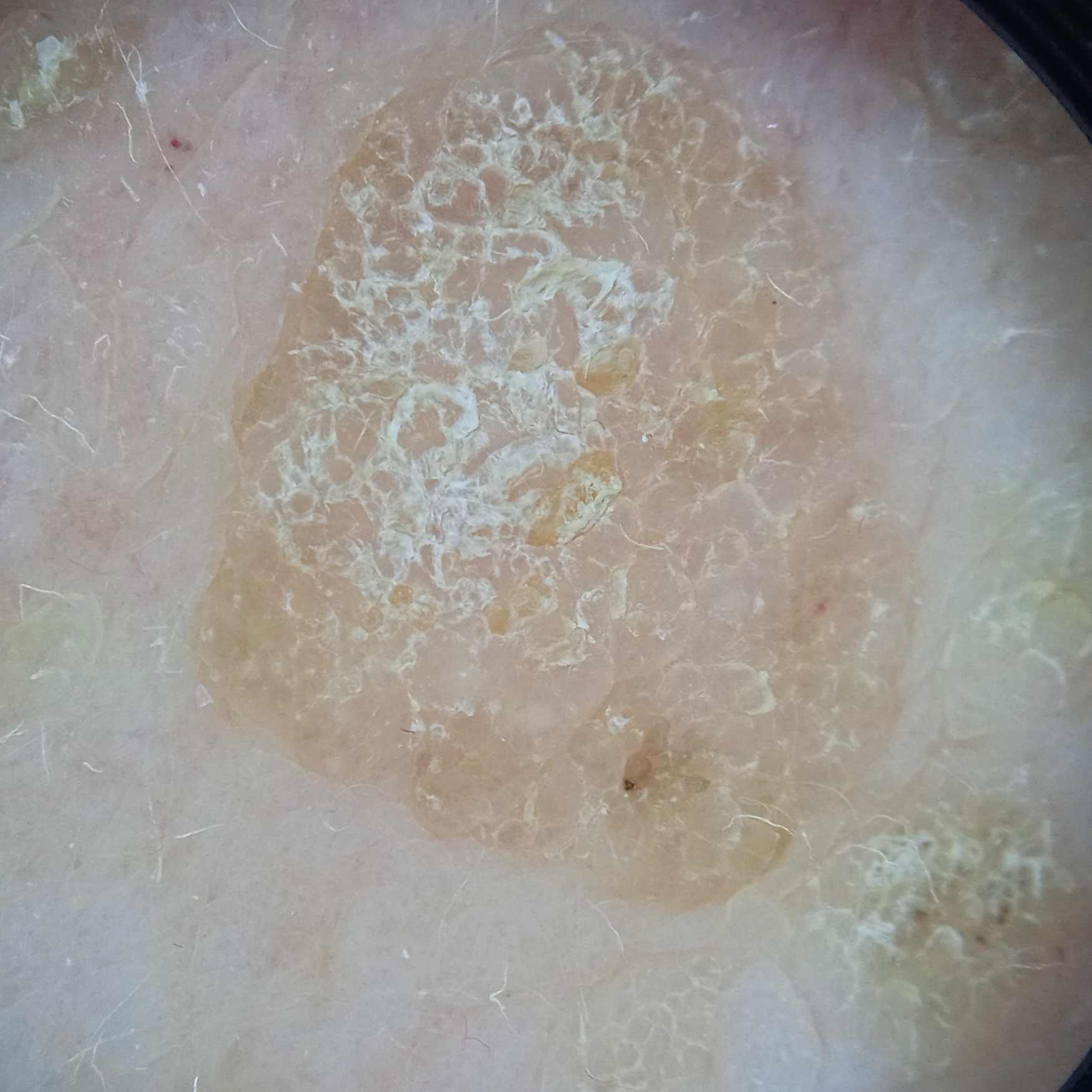{
  "patient": {
    "age": 55,
    "sex": "female"
  },
  "mole_burden": "a moderate number of melanocytic nevi",
  "image": "dermoscopic image",
  "sun_reaction": "skin reddens painfully with sun exposure",
  "risk_factors": {
    "positive": [
      "immunosuppression",
      "a prior organ transplant"
    ]
  },
  "lesion_location": "the back",
  "lesion_size": {
    "diameter_mm": 10.6
  },
  "diagnosis": {
    "name": "seborrheic keratosis",
    "malignancy": "benign"
  }
}